A dermatoscopic image of a skin lesion:
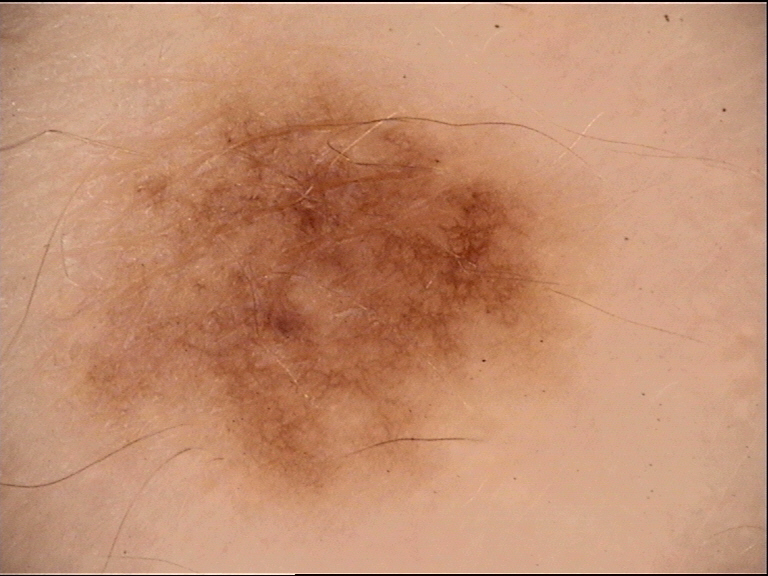Classified as a benign lesion — a dysplastic junctional nevus.